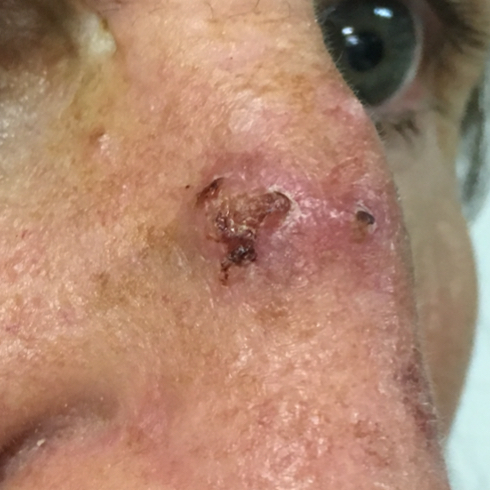Diagnosis: Histopathology confirmed a basal cell carcinoma.